The photo was captured at a distance: 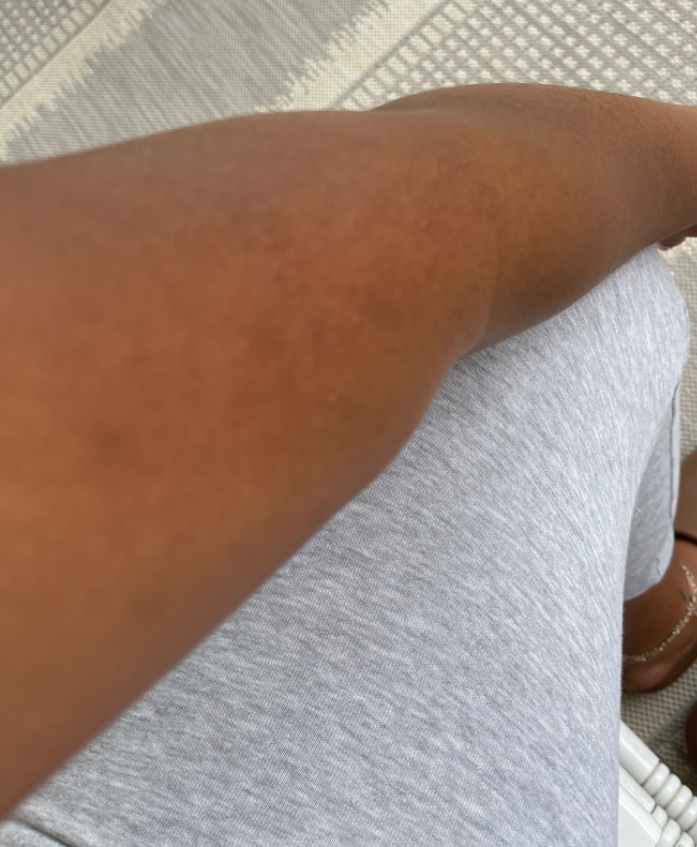The reviewing dermatologist was unable to assign a differential diagnosis from the image.